A dermoscopic photograph of a skin lesion.
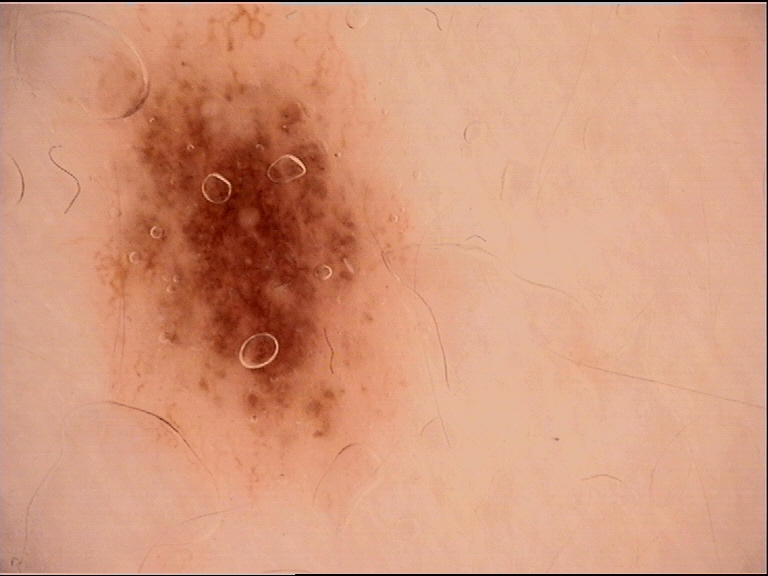Conclusion: The diagnosis was a dysplastic junctional nevus.